This is a dermoscopic photograph of a skin lesion.
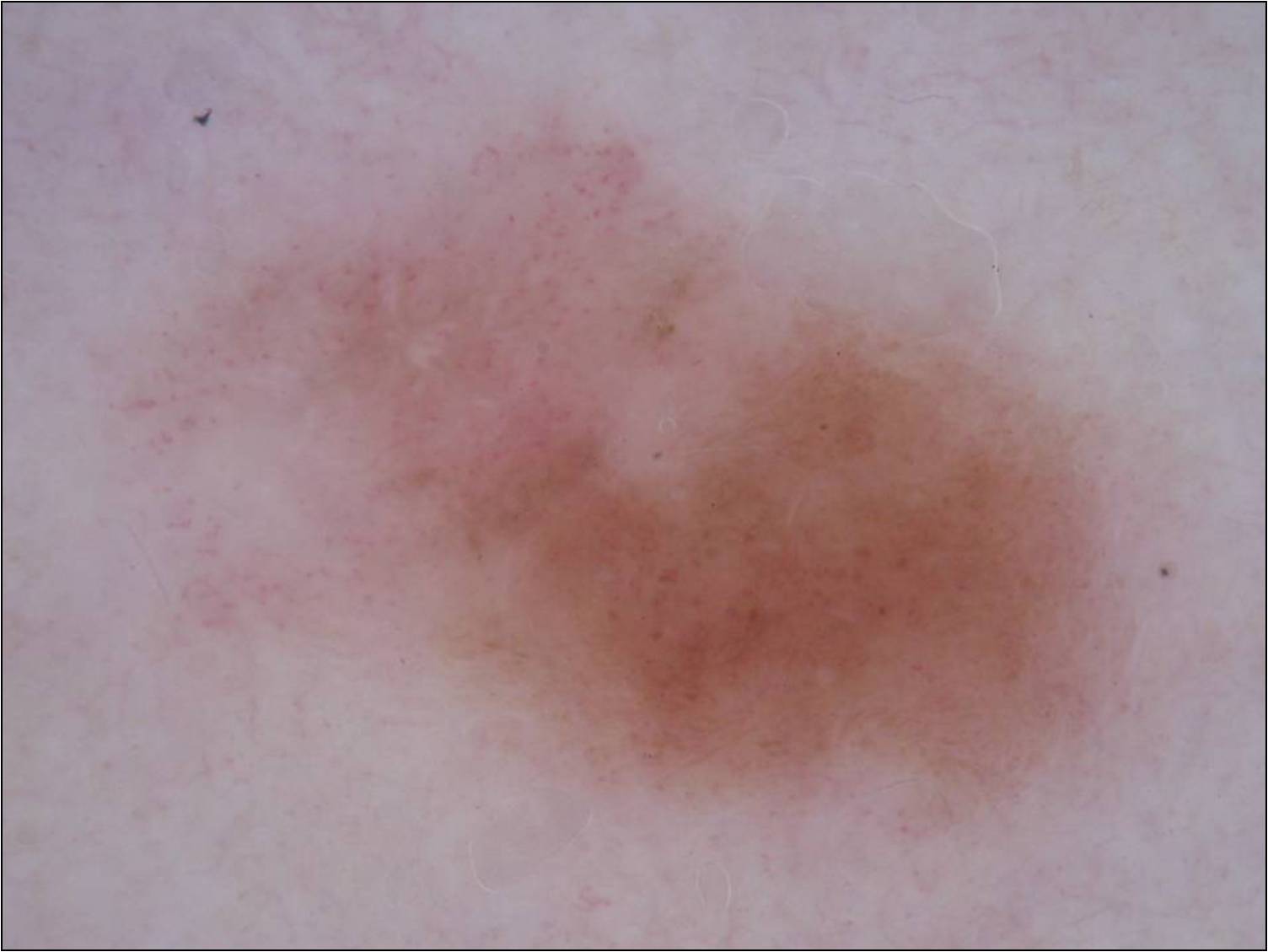As (left, top, right, bottom), the lesion's extent is 67, 74, 1231, 893. The lesion takes up a large portion of the image. The dermoscopic pattern shows globules. Confirmed on histopathology as a melanoma.